Texture is reported as raised or bumpy. The lesion involves the arm. The lesion is associated with itching. The patient described the issue as a rash. This is a close-up image. The patient reports the condition has been present for less than one week. The patient reported no systemic symptoms: 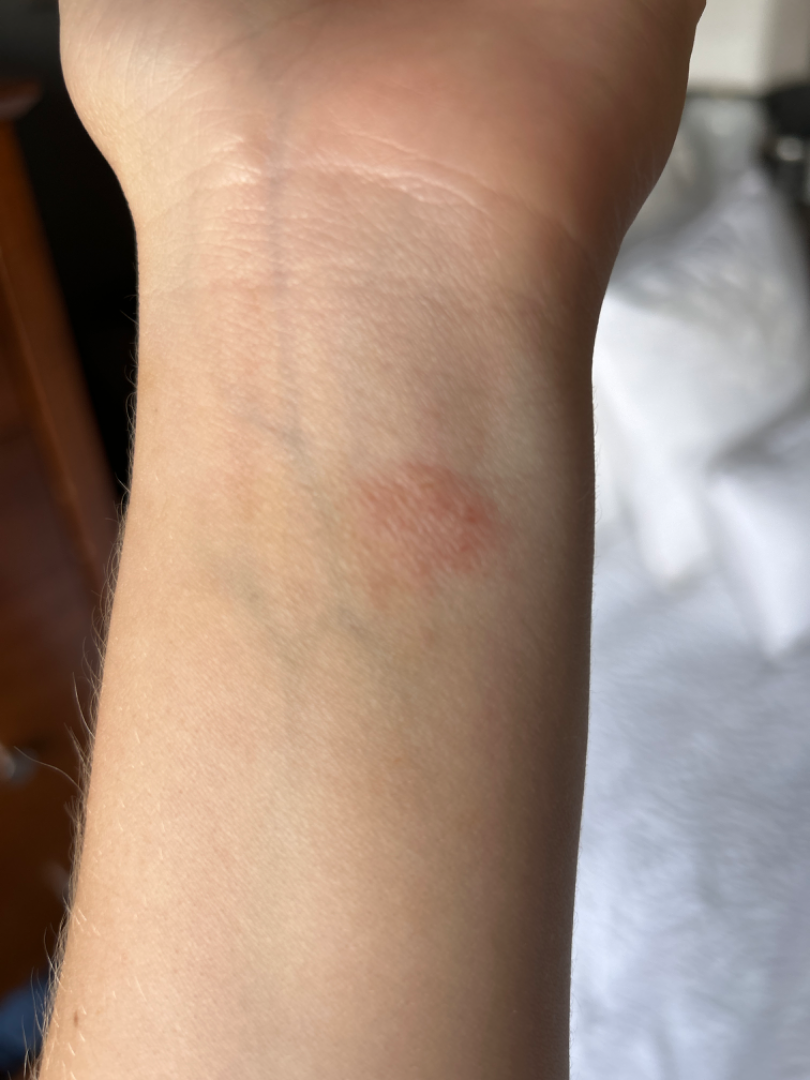assessment: ungradable on photographic review